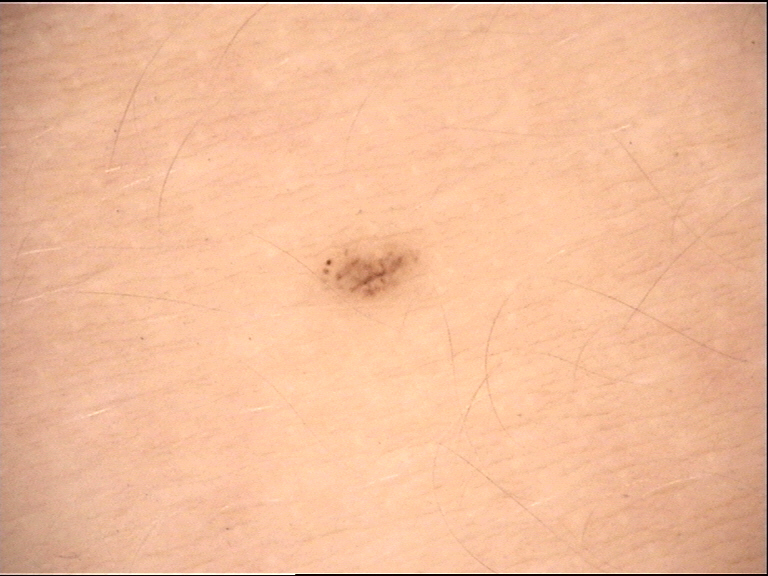modality: dermatoscopy; assessment: junctional nevus (expert consensus).